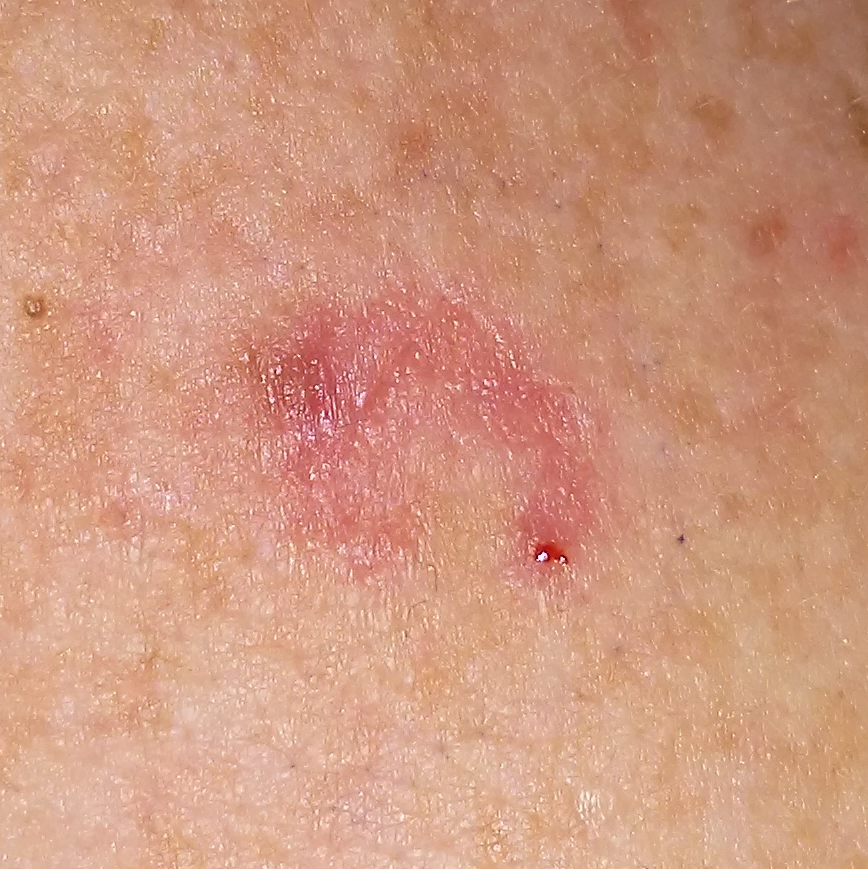A clinical close-up photograph of a skin lesion. Fitzpatrick I. The lesion is on the back. Measuring about 12 × 8 mm. No symptoms reported. On biopsy, the diagnosis was a malignancy — a basal cell carcinoma.